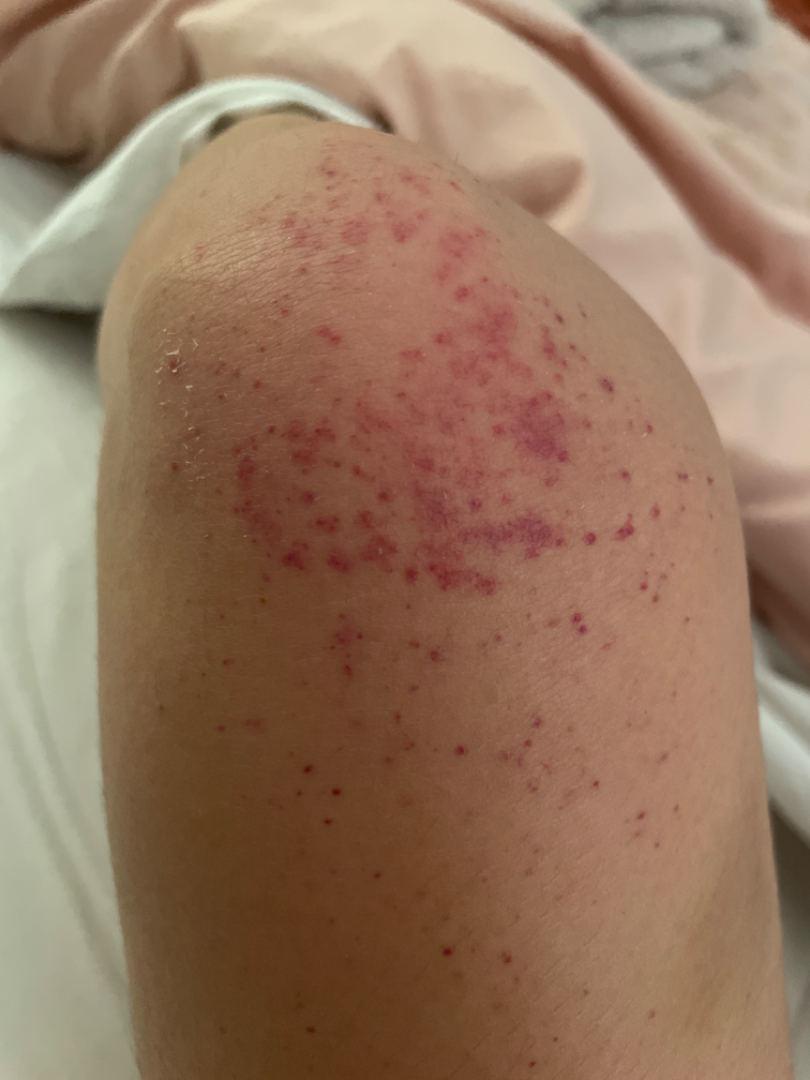Impression:
The image was not sufficient for the reviewer to characterize the skin condition.